No constitutional symptoms were reported; the photo was captured at an angle; texture is reported as raised or bumpy; present for less than one week; the lesion is associated with itching and burning; the arm is involved; self-categorized by the patient as a rash: 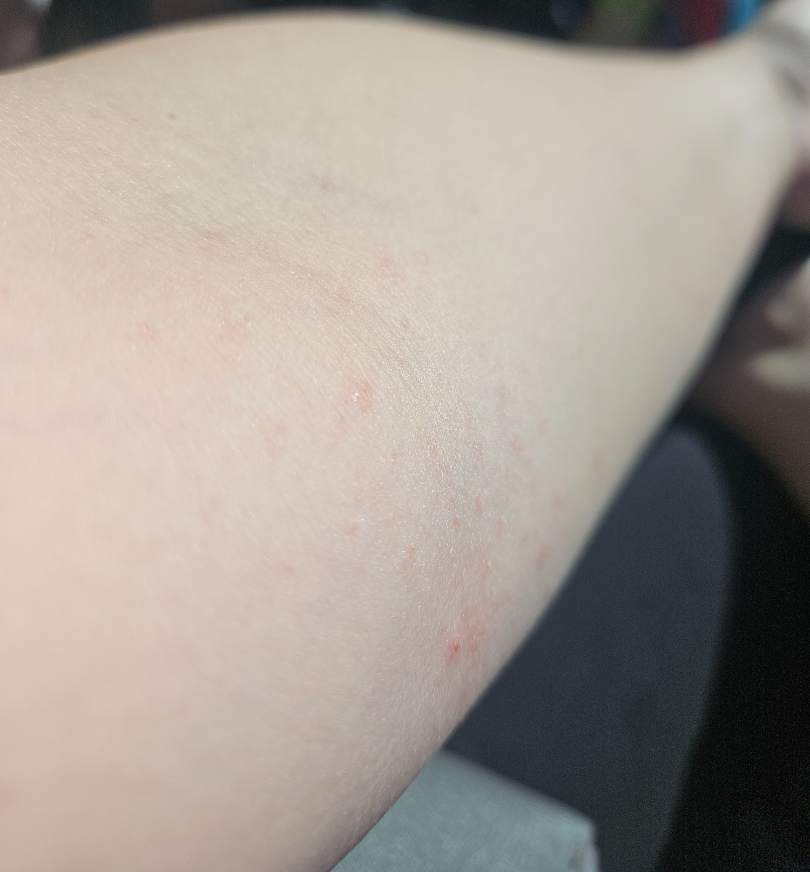On remote dermatologist review: Eczema (100%).